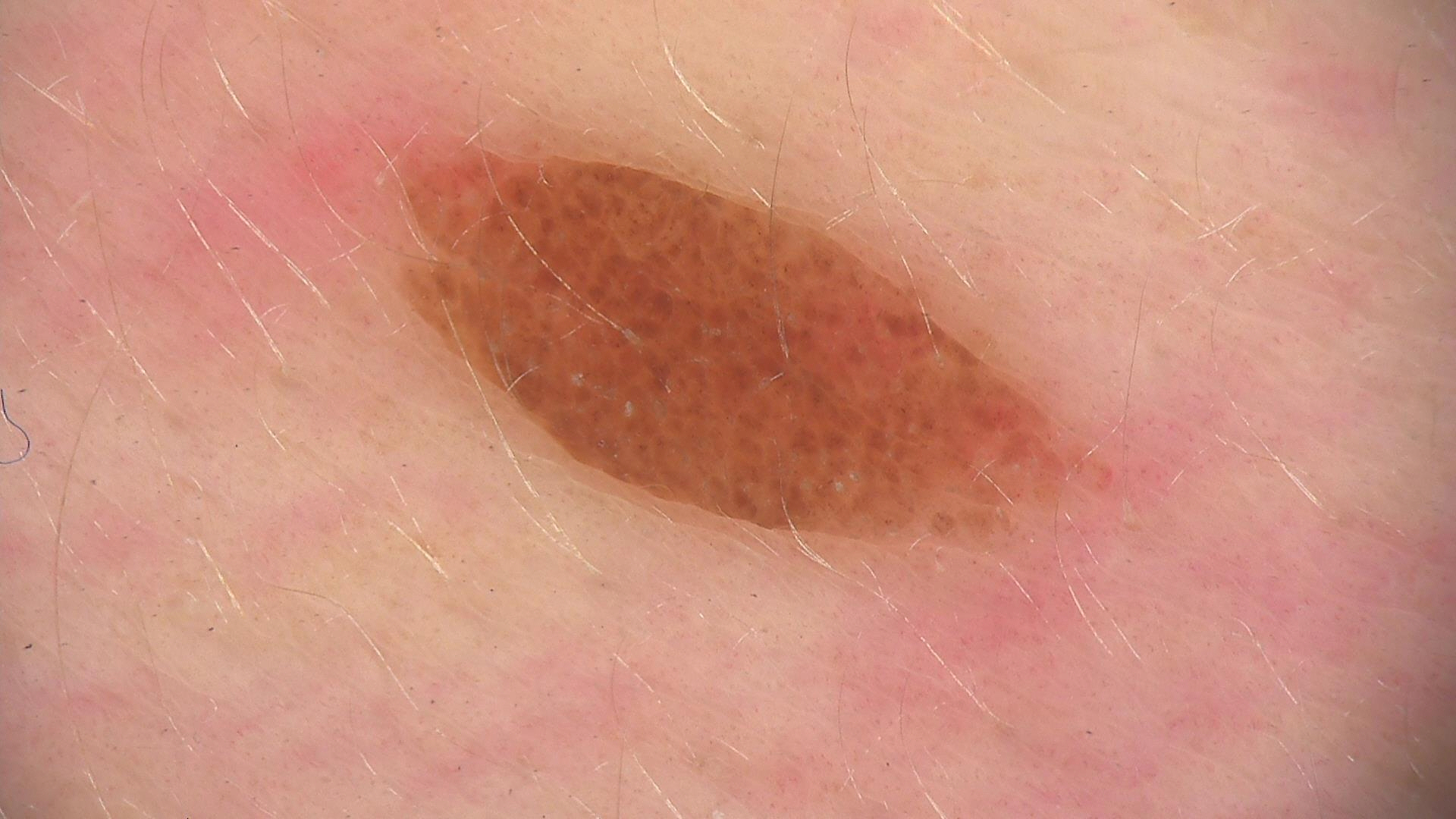Summary:
This is a banal lesion.
Impression:
Labeled as a compound nevus.